A male patient age 58. A clinical photograph of a skin lesion. The patient is skin type II — 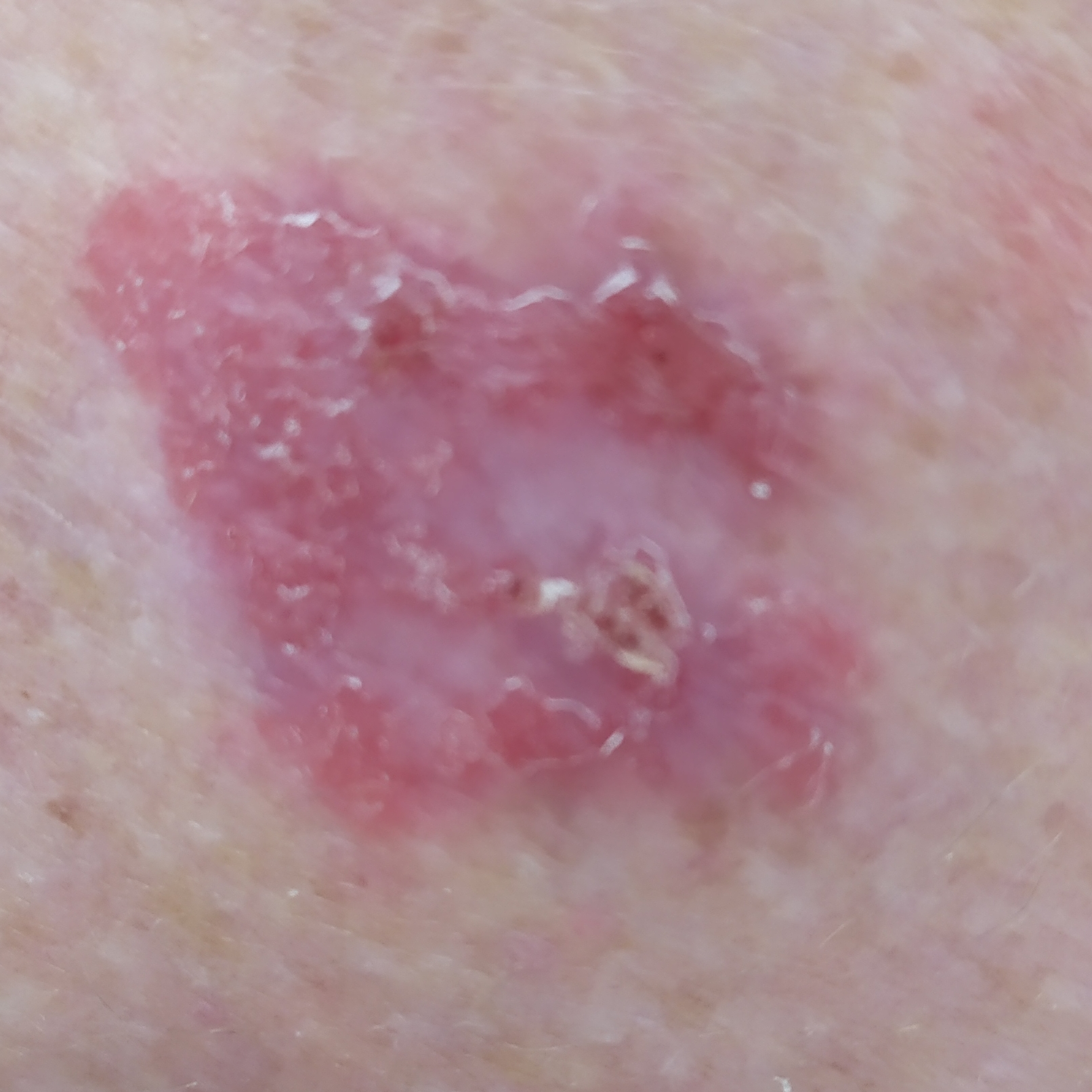The lesion is located on the back.
The lesion measures 30 × 20 mm.
Per patient report, the lesion itches.
Histopathology confirmed a malignant lesion — a squamous cell carcinoma.